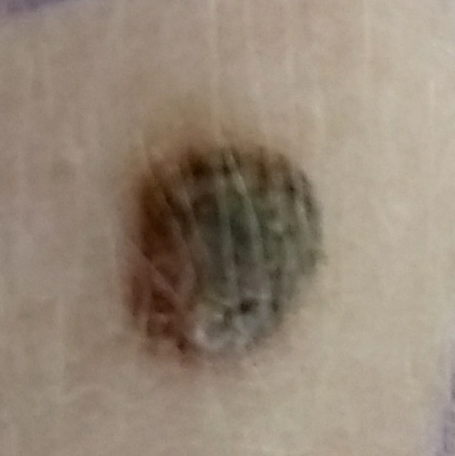Q: What kind of image is this?
A: smartphone clinical photo
Q: What does the exposure history note?
A: prior malignancy (patient or family)
Q: What is the patient's skin type?
A: I
Q: Tell me about the patient.
A: female, 17 years old
Q: Where on the body is the lesion?
A: an arm
Q: What are the lesion's dimensions?
A: 7 × 7 mm
Q: Any reported symptoms?
A: elevation / no pain
Q: What is the diagnosis?
A: nevus (biopsy-proven)